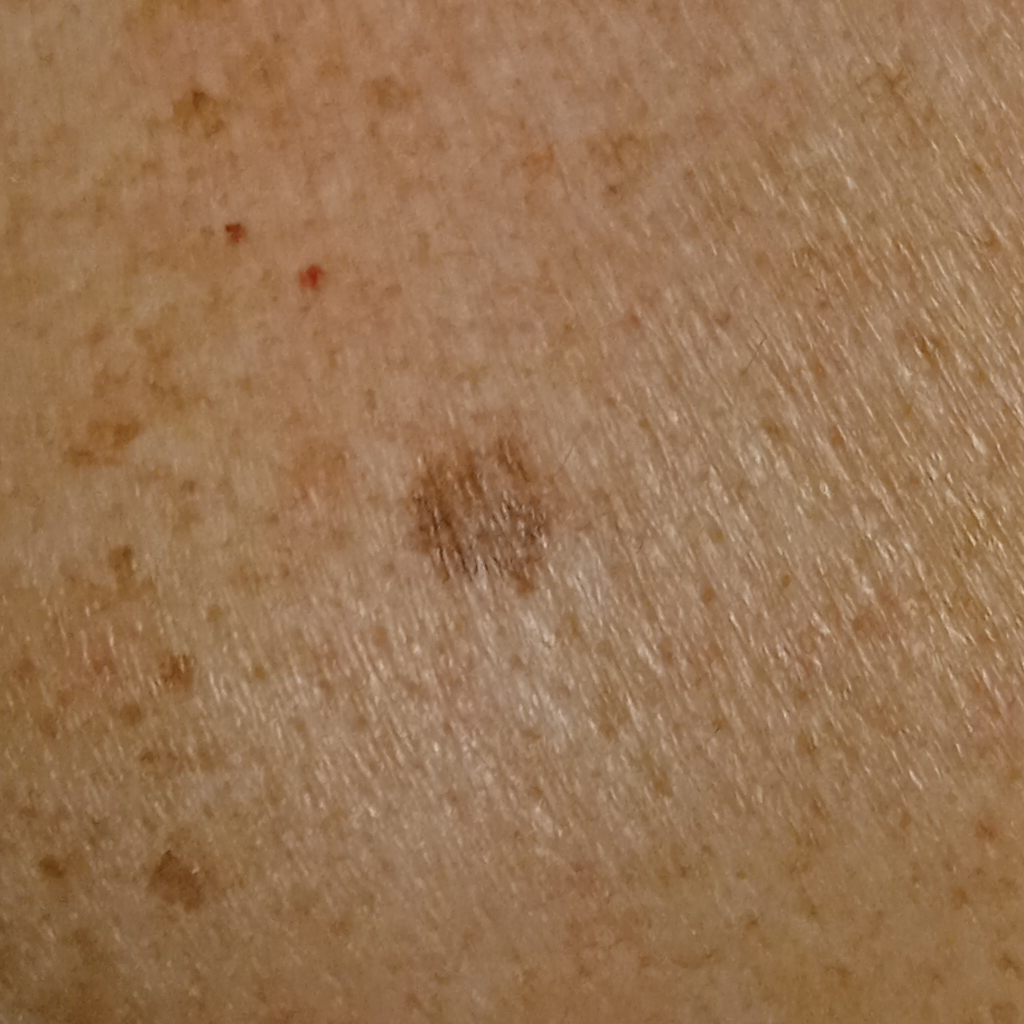The reviewing dermatologists could not reach a confident diagnosis. {
  "referral": "research study (no referral diagnosis)",
  "image": "clinical photo",
  "patient": {
    "age": 81,
    "sex": "male"
  },
  "lesion_location": "the back"
}